A dermoscopic image of a skin lesion:
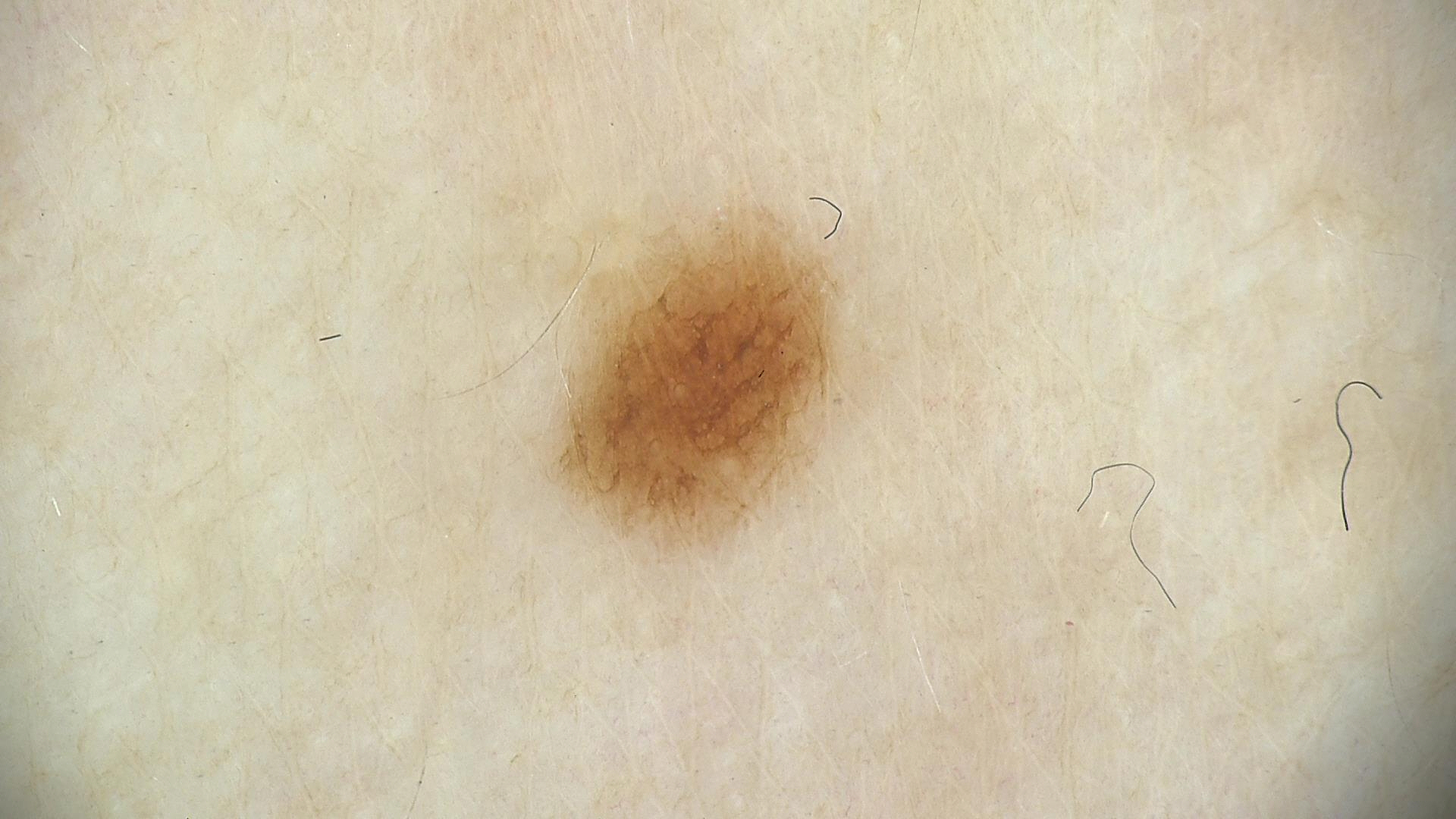| feature | finding |
|---|---|
| diagnosis | dysplastic junctional nevus (expert consensus) |